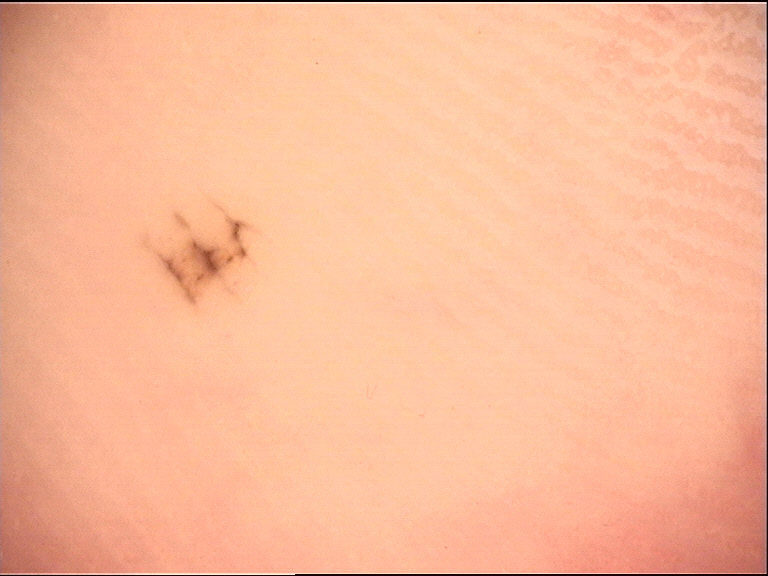Findings:
A dermoscopy image of a single skin lesion.
Conclusion:
Labeled as an acral dysplastic junctional nevus.